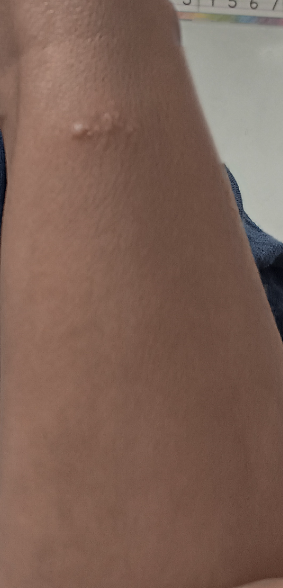Q: What was the assessment?
A: ungradable on photographic review
Q: How was the photo taken?
A: close-up